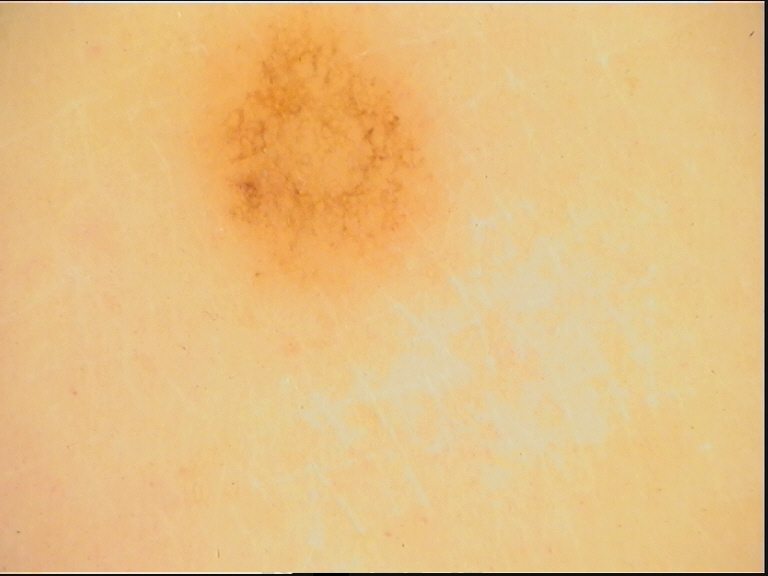diagnostic label: dysplastic junctional nevus (expert consensus)